Dermoscopy of a skin lesion.
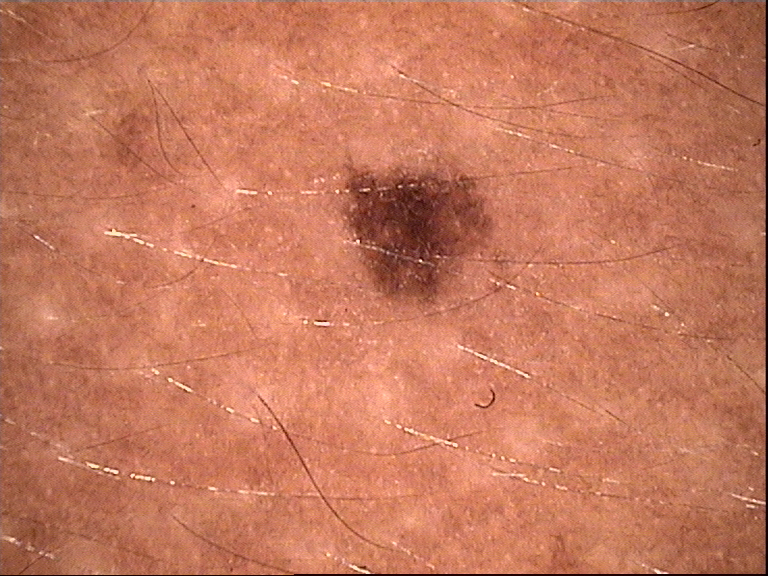Classified as a dysplastic junctional nevus.